A skin lesion imaged with a dermatoscope:
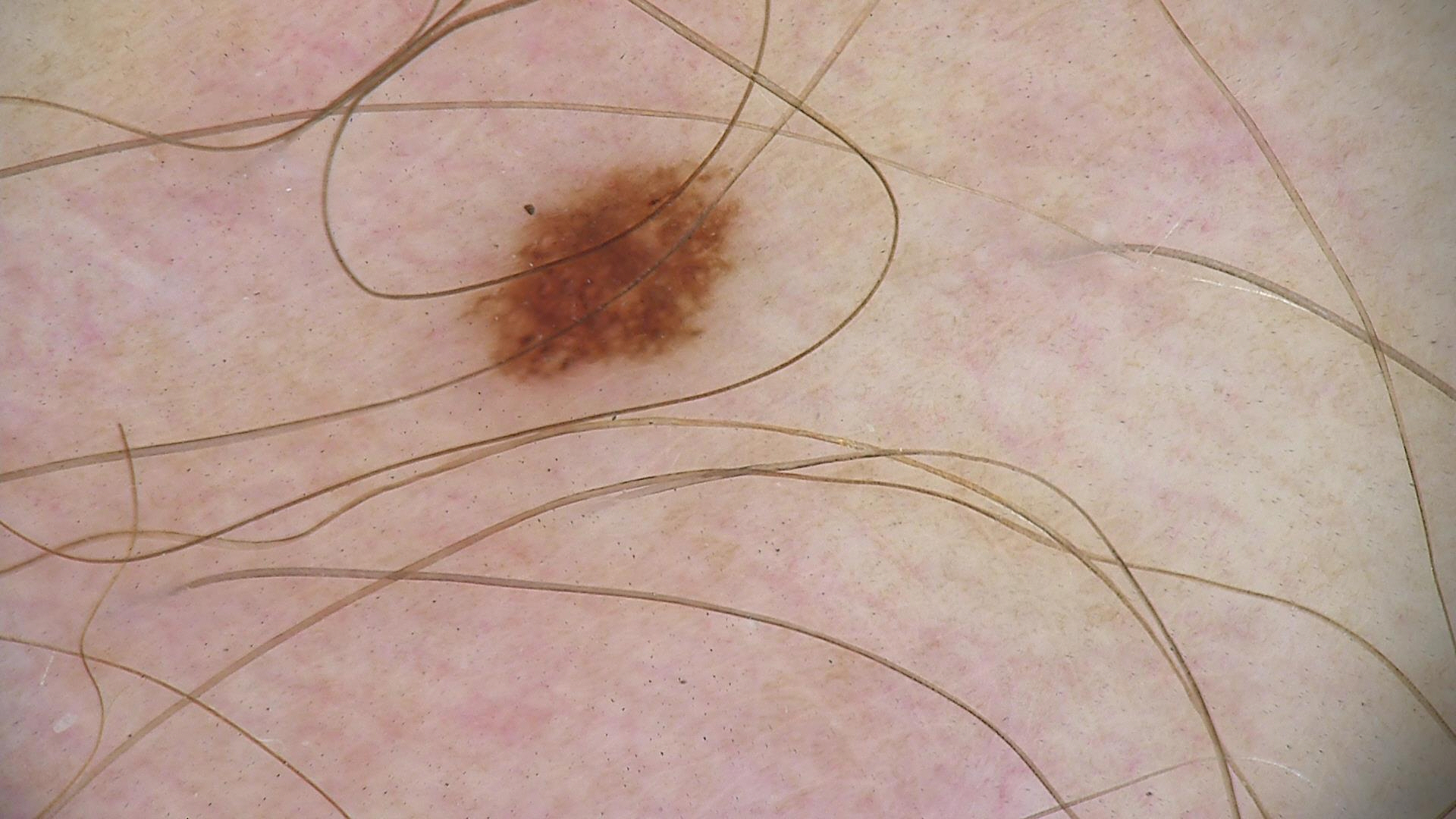Labeled as a benign lesion — a dysplastic junctional nevus.